A dermoscopy image of a single skin lesion:
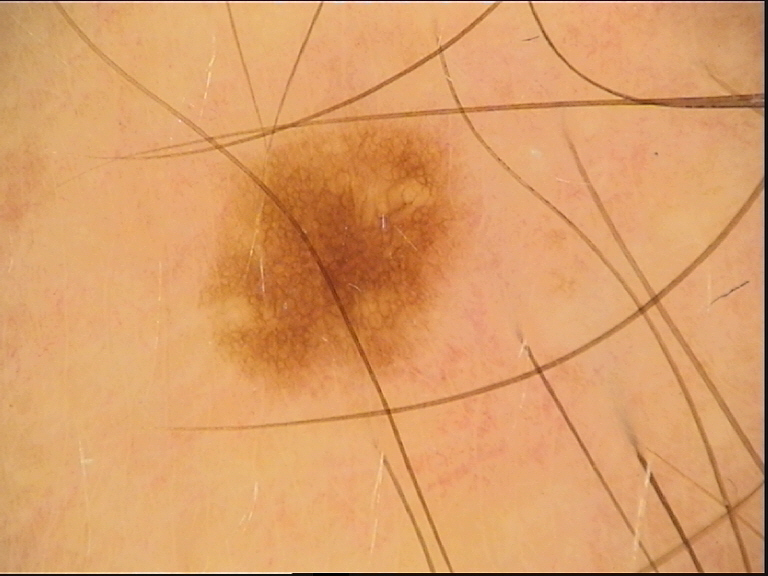This is a banal lesion. Labeled as a junctional nevus.